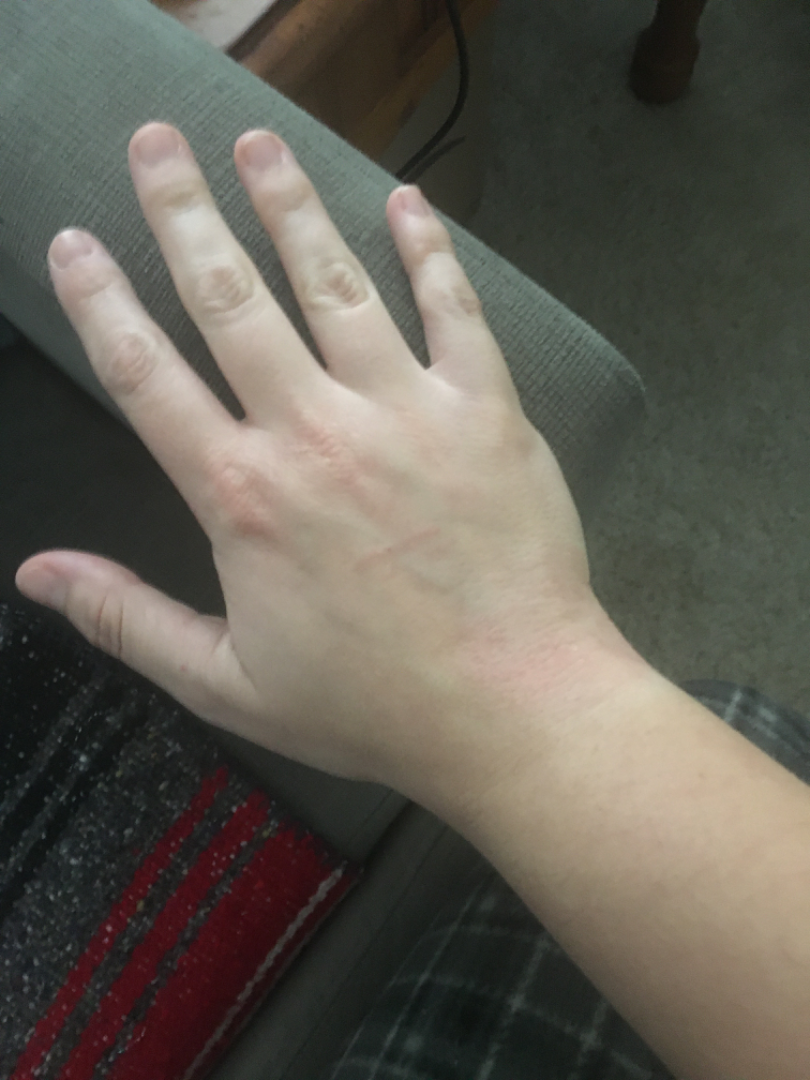On photographic review, most likely Eczema; the differential also includes Irritant Contact Dermatitis.